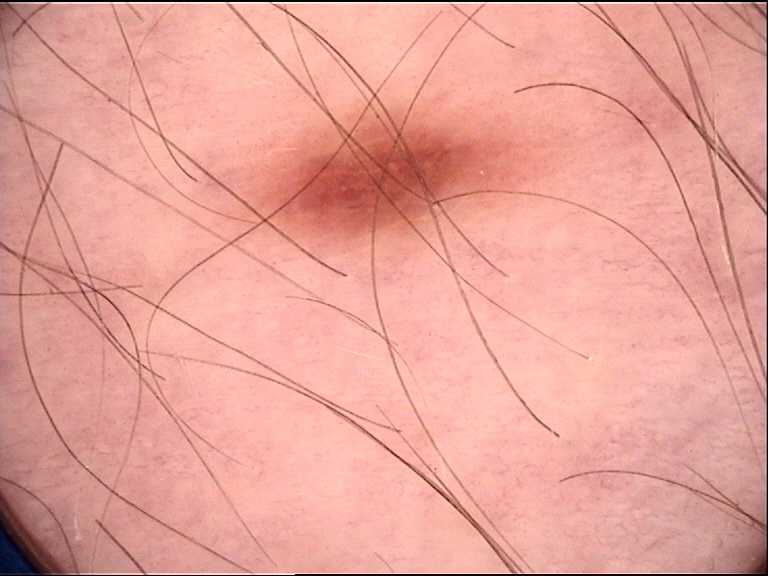Classified as a dysplastic junctional nevus.